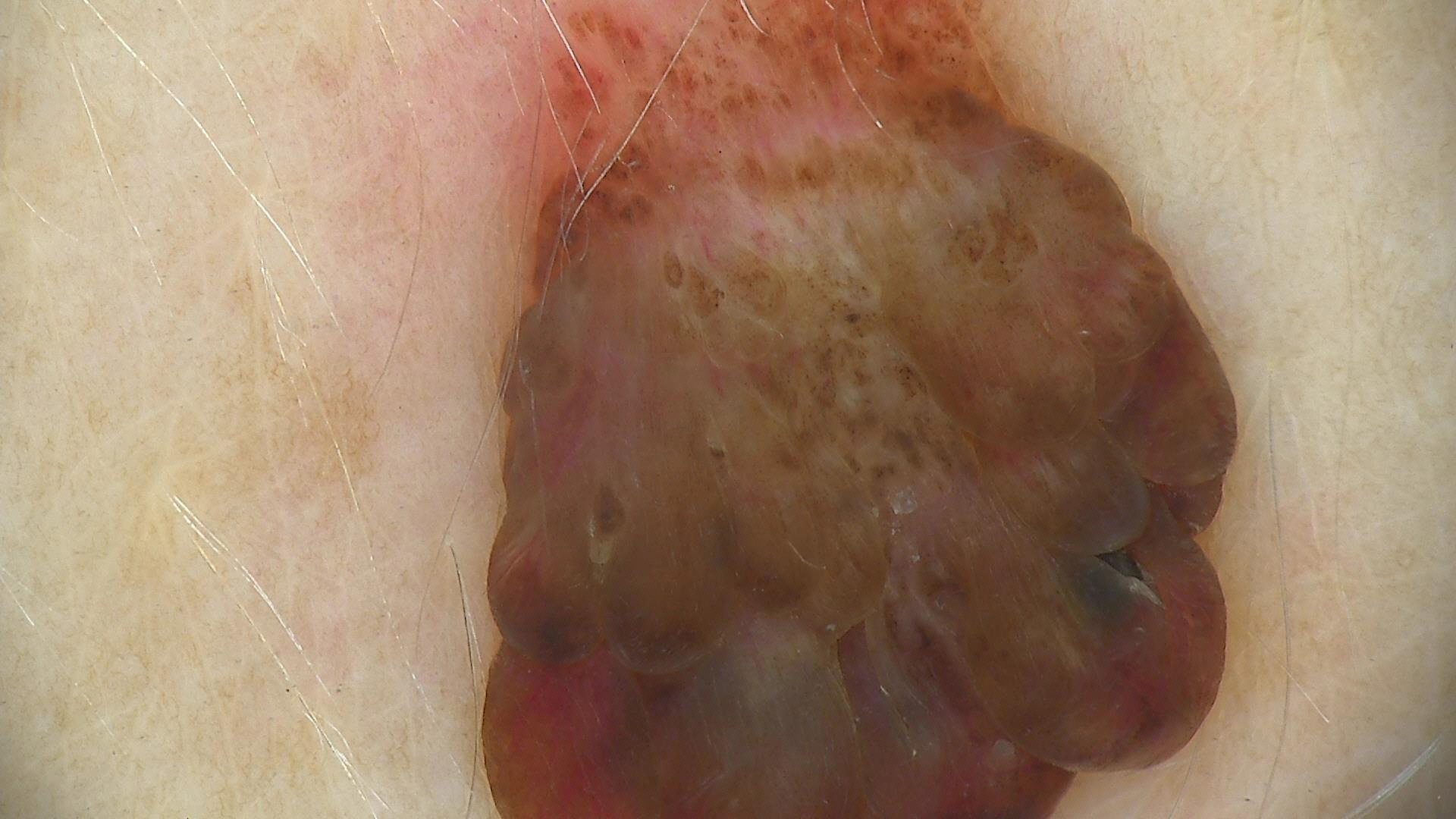diagnostic label = dermal nevus (expert consensus)